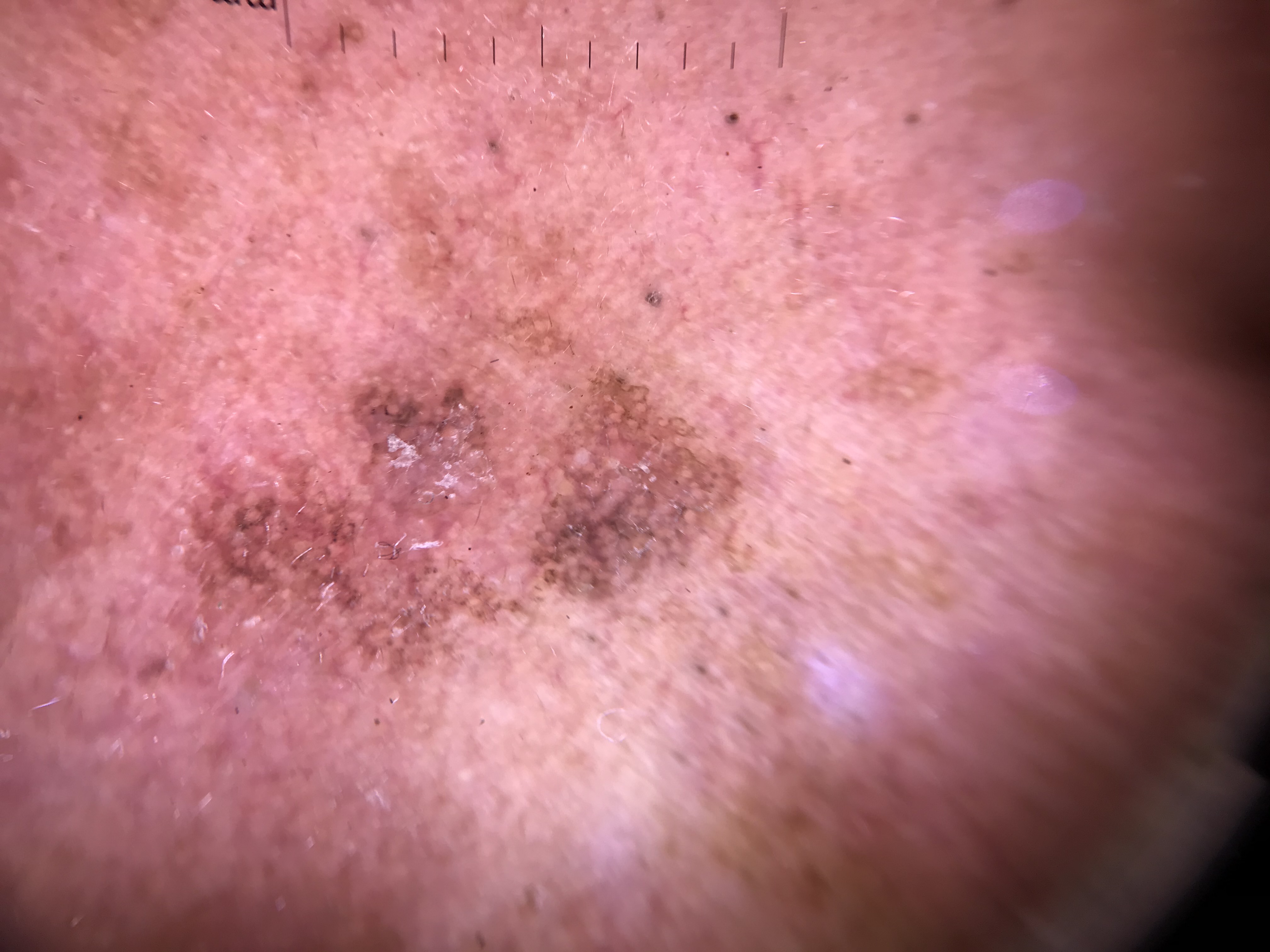Labeled as a seborrheic keratosis.